This is a dermoscopic photograph of a skin lesion · the subject is a female roughly 50 years of age.
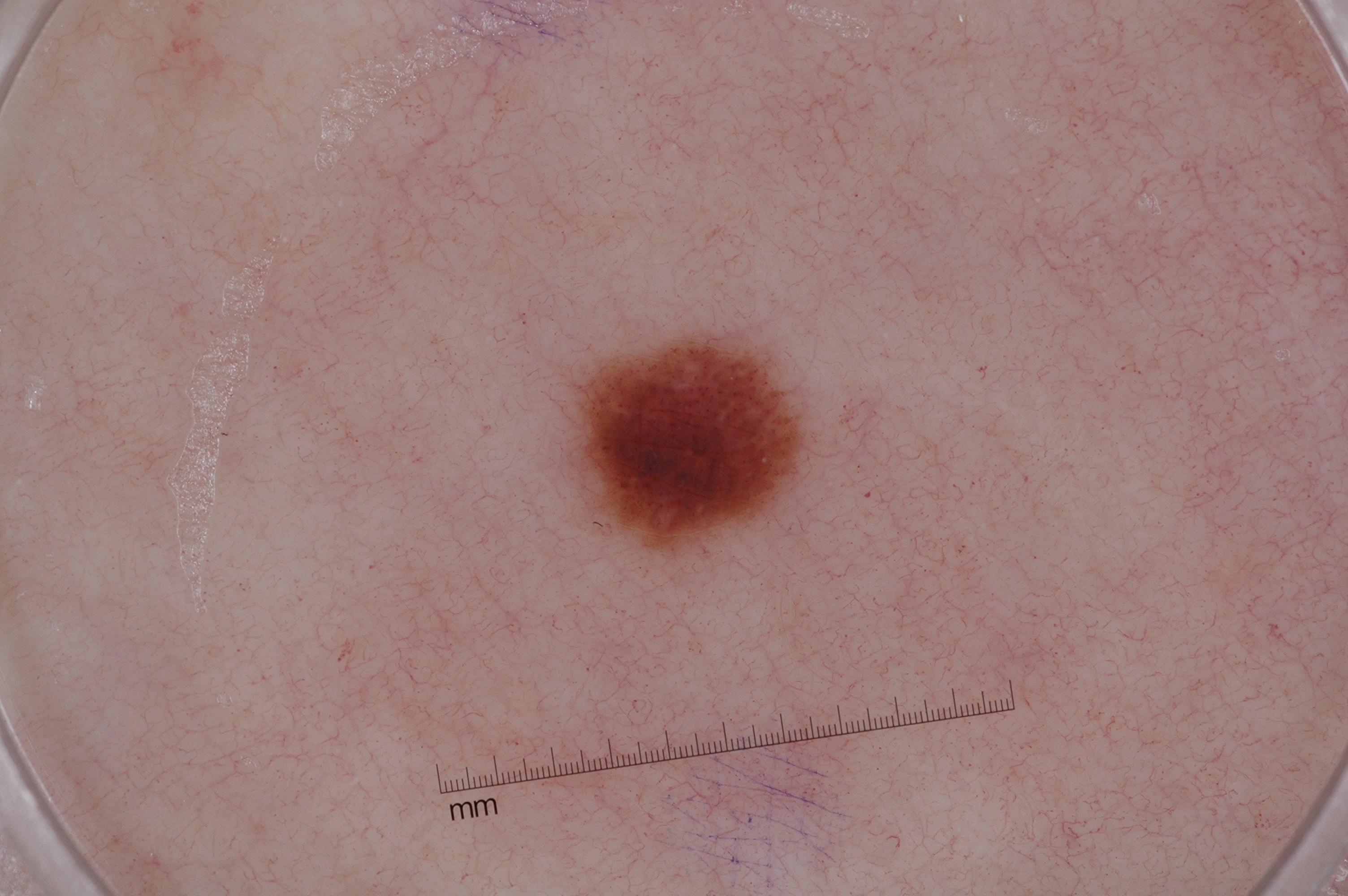Q: How large is the lesion within the image?
A: small
Q: Which dermoscopic features were noted?
A: negative network
Q: What is the lesion's bounding box?
A: bbox(579, 336, 801, 553)
Q: What is the diagnosis?
A: a melanocytic nevus